The lesion involves the arm, head or neck, front of the torso and back of the hand; this is a close-up image:
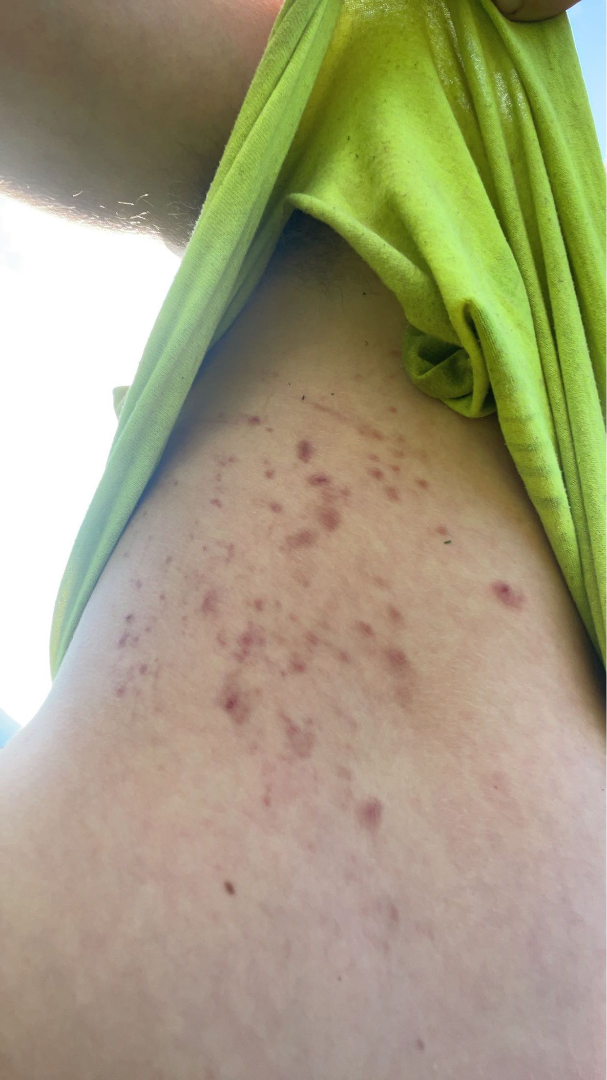skin_tone:
  fitzpatrick: IV
  monk_skin_tone:
    - 1
    - 2
patient_category: a rash
duration: less than one week
texture: flat
symptoms: itching
differential:
  leading:
    - Acne
  considered:
    - Folliculitis